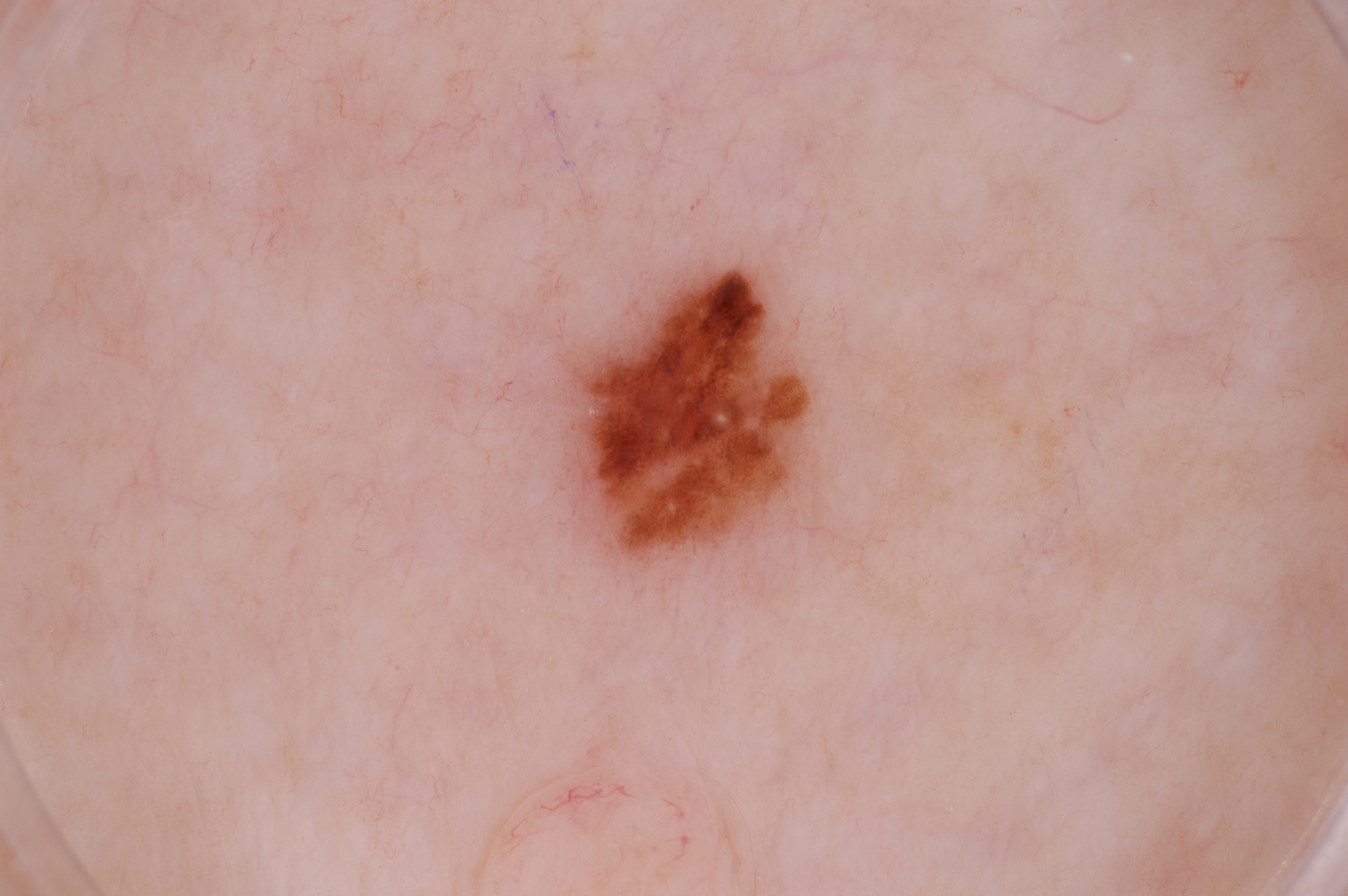A male patient aged 78-82.
A dermoscopic close-up of a skin lesion.
In (x1, y1, x2, y2) order, the lesion is located at (555, 260, 818, 571).
The lesion covers approximately 4% of the dermoscopic field.
Dermoscopy demonstrates pigment network and milia-like cysts.
The lesion was assessed as a melanocytic nevus, a benign lesion.